Reported lesion symptoms include burning and pain. Present for about one day. The lesion is described as raised or bumpy. The affected area is the head or neck. This image was taken at a distance. No constitutional symptoms were reported: 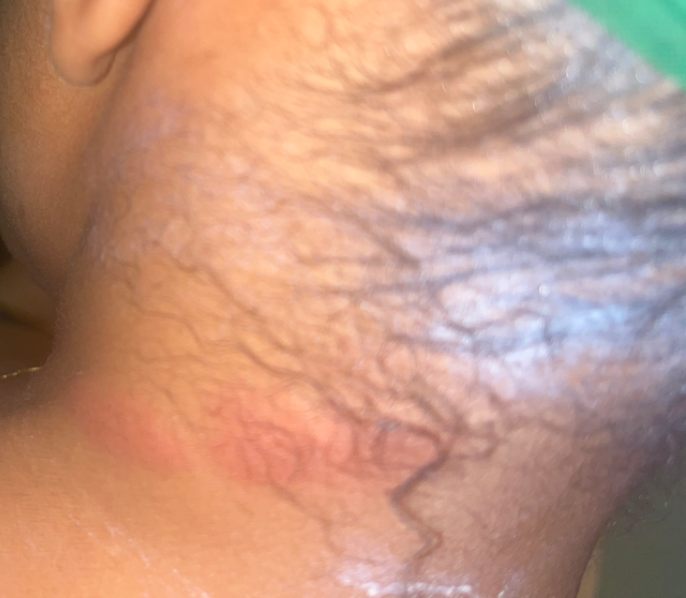Findings:
* assessment: indeterminate